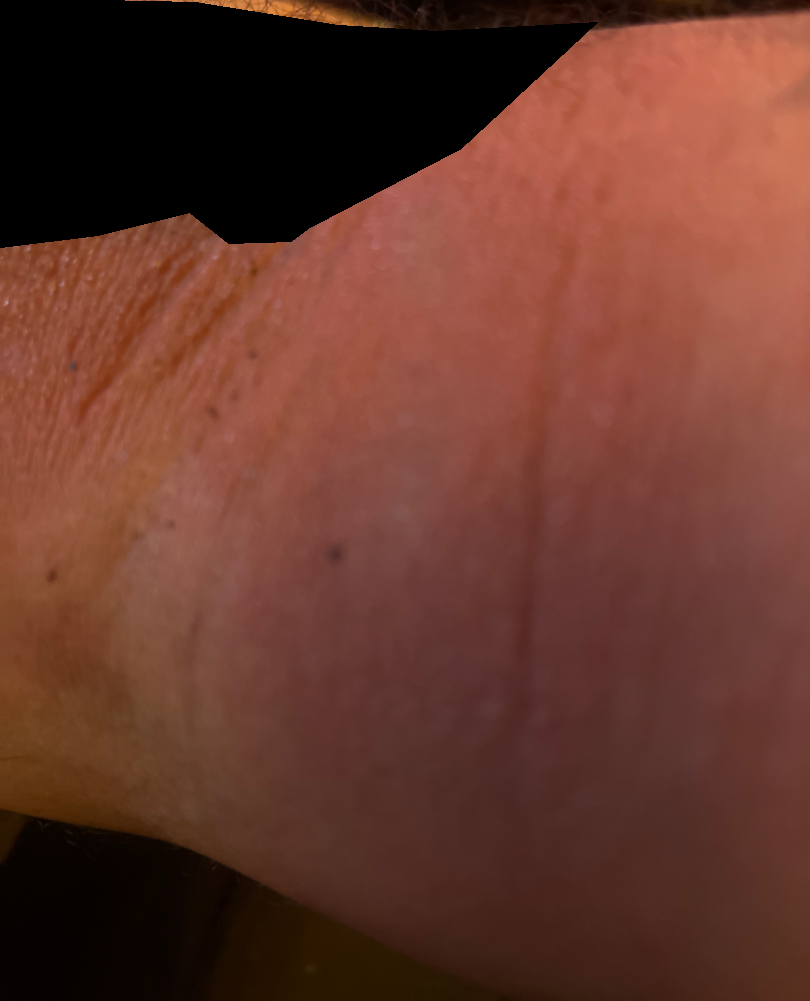Notes:
* present for — one to four weeks
* reported symptoms — burning, enlargement, darkening, itching and bothersome appearance
* patient — male
* skin tone — Fitzpatrick IV
* surface texture — fluid-filled
* body site — arm
* self-categorized as — a rash
* image framing — at an angle
* differential diagnosis — three independent reviewers: Cellulitis, Eczema and Allergic Contact Dermatitis were each considered, in no particular order